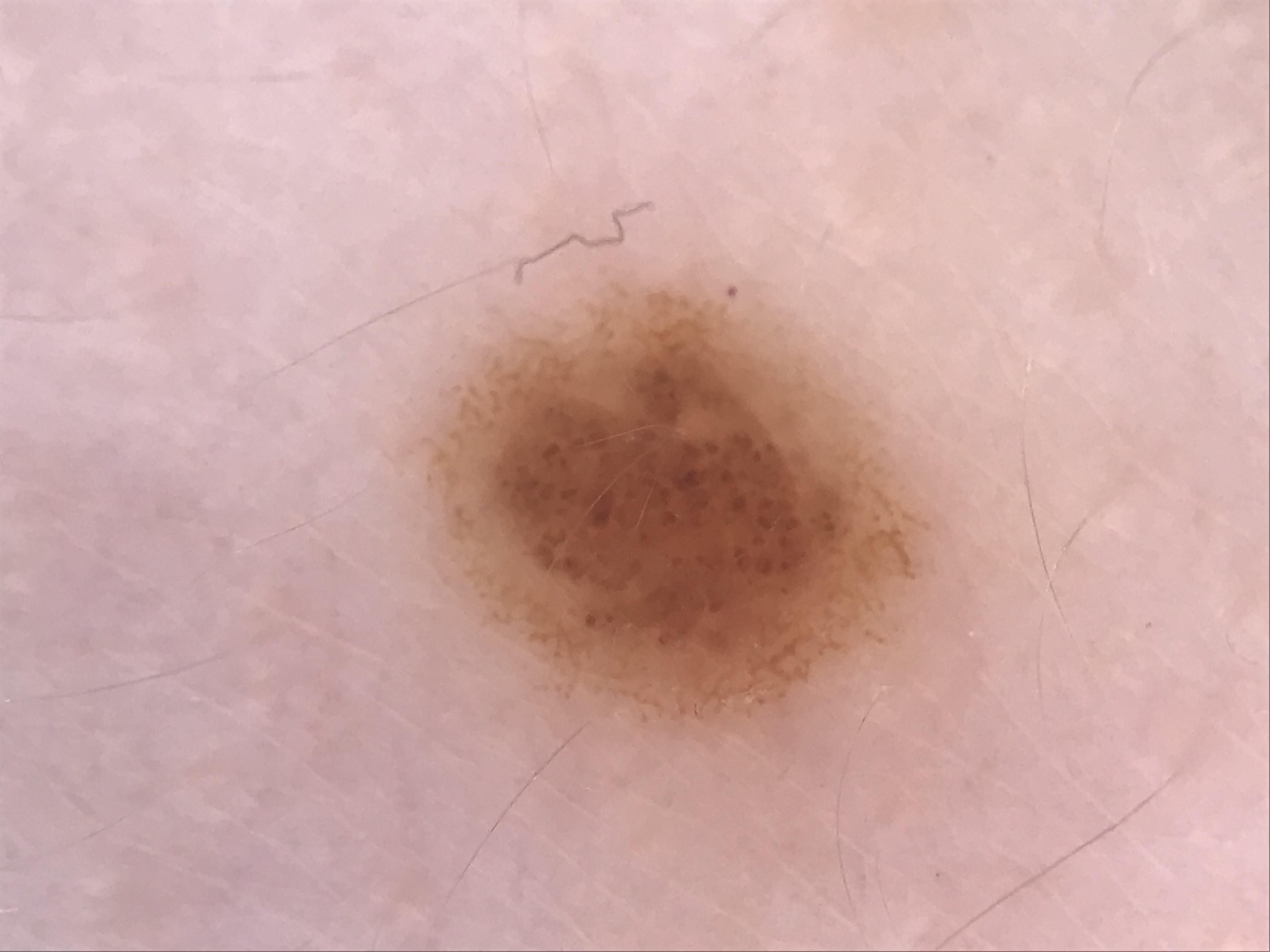A dermoscopic image of a skin lesion. Labeled as a benign lesion — a dysplastic compound nevus.